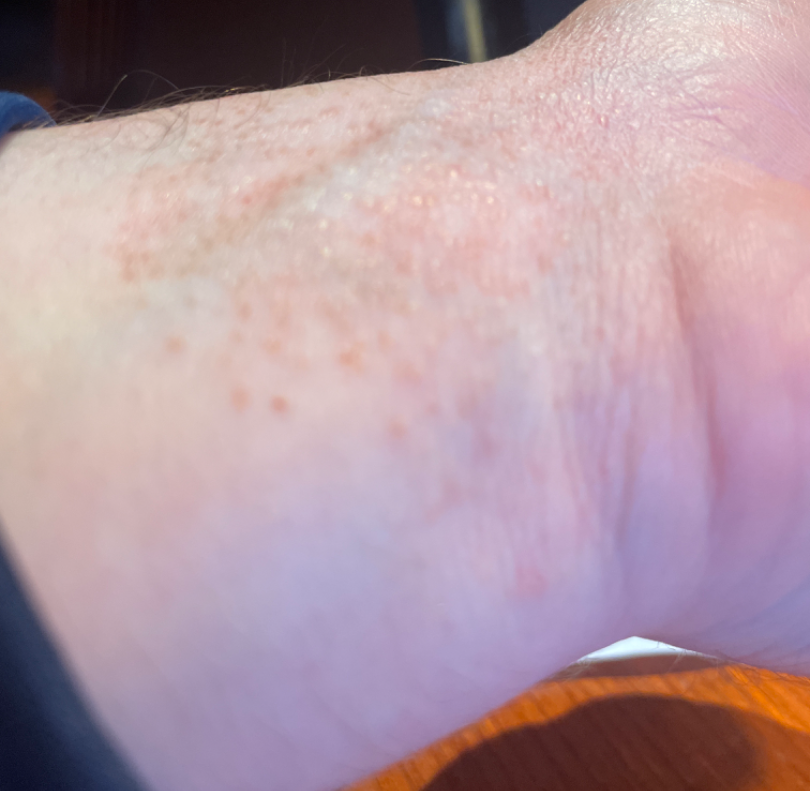shot type — at an angle | clinical impression — Eczema (favored); Lichen planus/lichenoid eruption (possible).